The photograph was taken at an angle · the lesion involves the back of the torso: 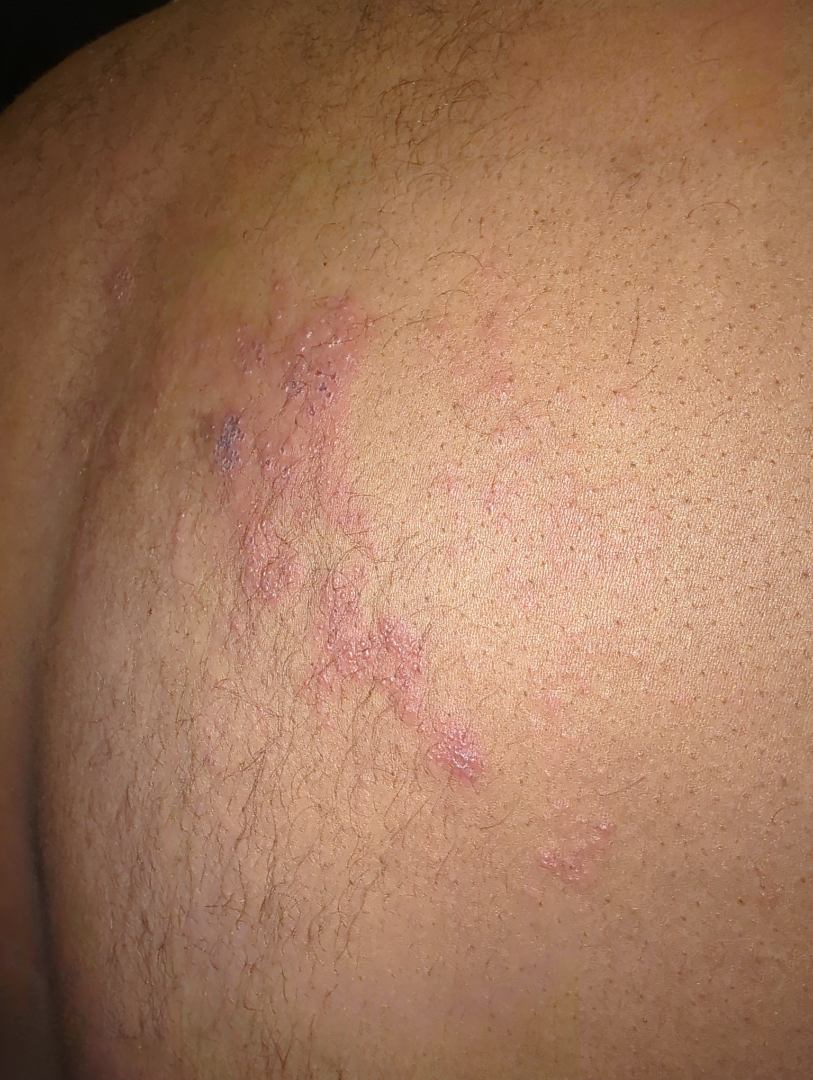Most consistent with Herpes Zoster.